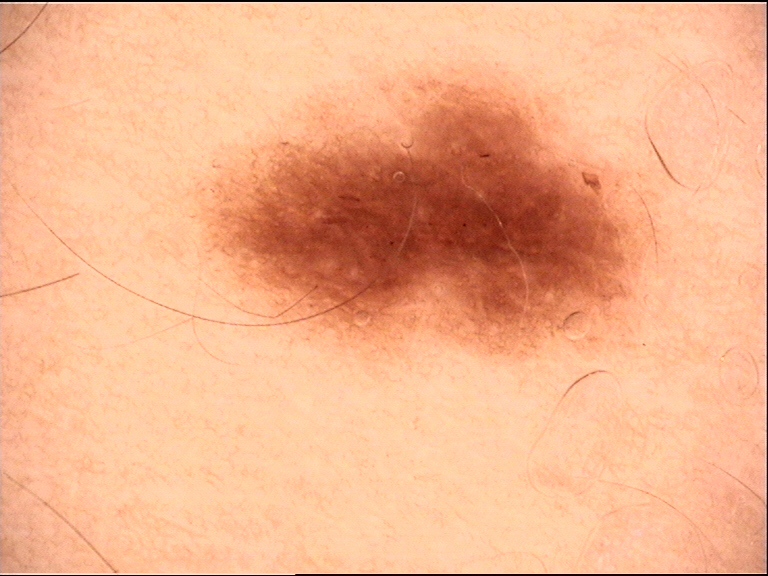The diagnostic label was a junctional nevus.